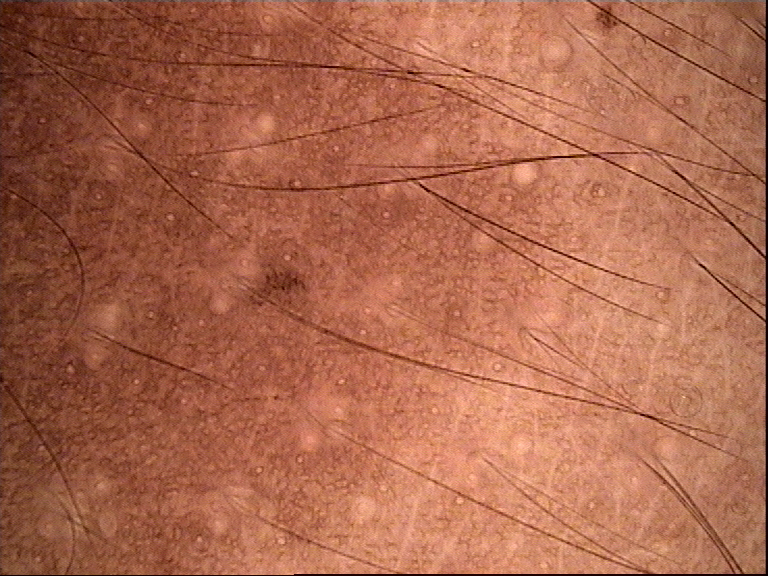The diagnostic label was a congenital junctional nevus.